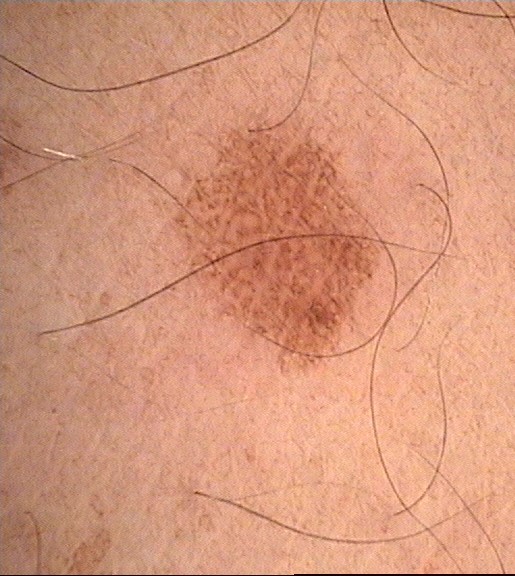imaging: dermoscopy; class: dysplastic junctional nevus (expert consensus).